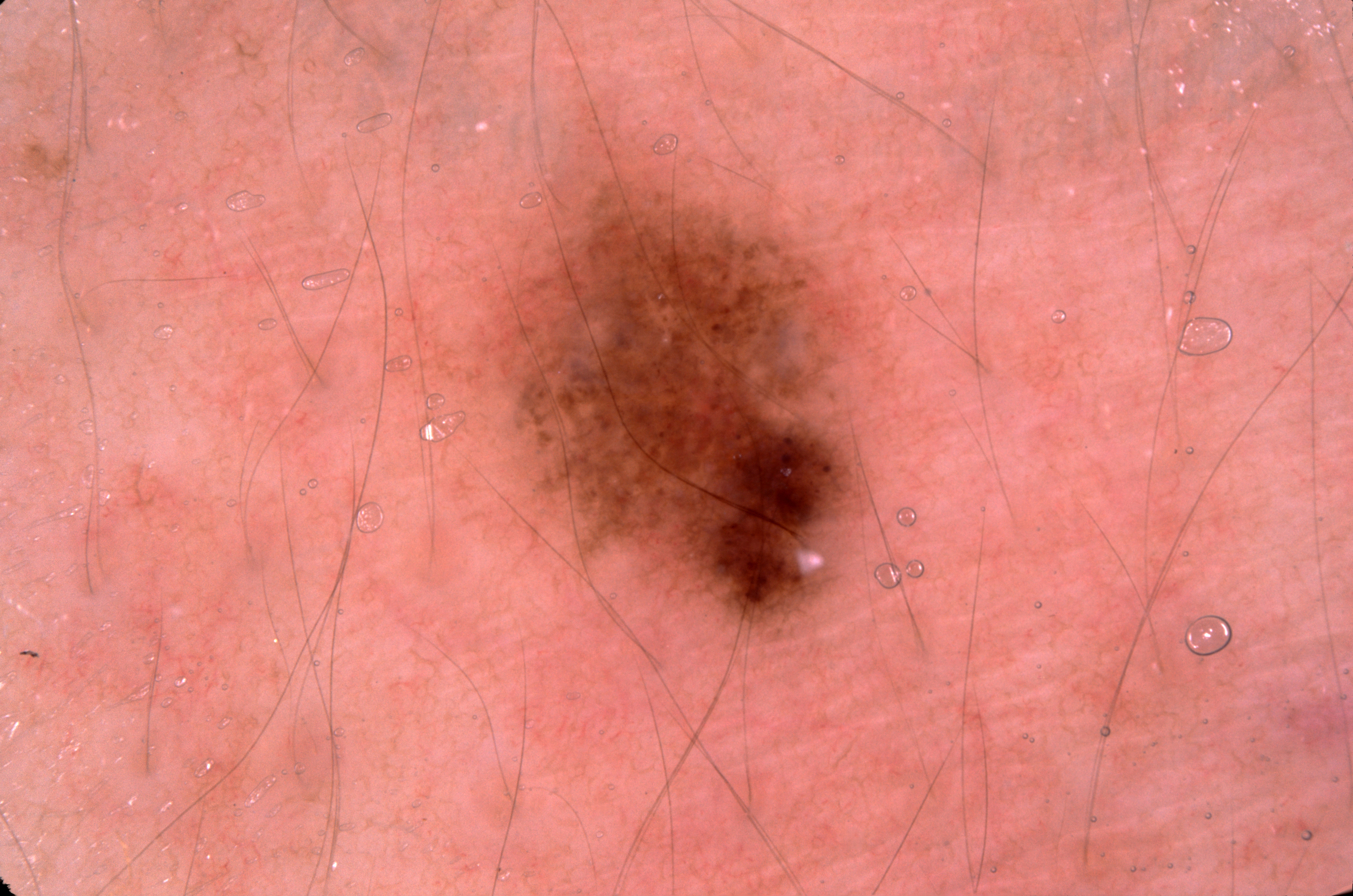Dermoscopy of a skin lesion.
A mid-sized lesion within the field.
Dermoscopically, the lesion shows pigment network and milia-like cysts.
In (x1, y1, x2, y2) order, the lesion spans bbox(486, 147, 877, 623).
The diagnostic assessment was a melanocytic nevus, a benign lesion.